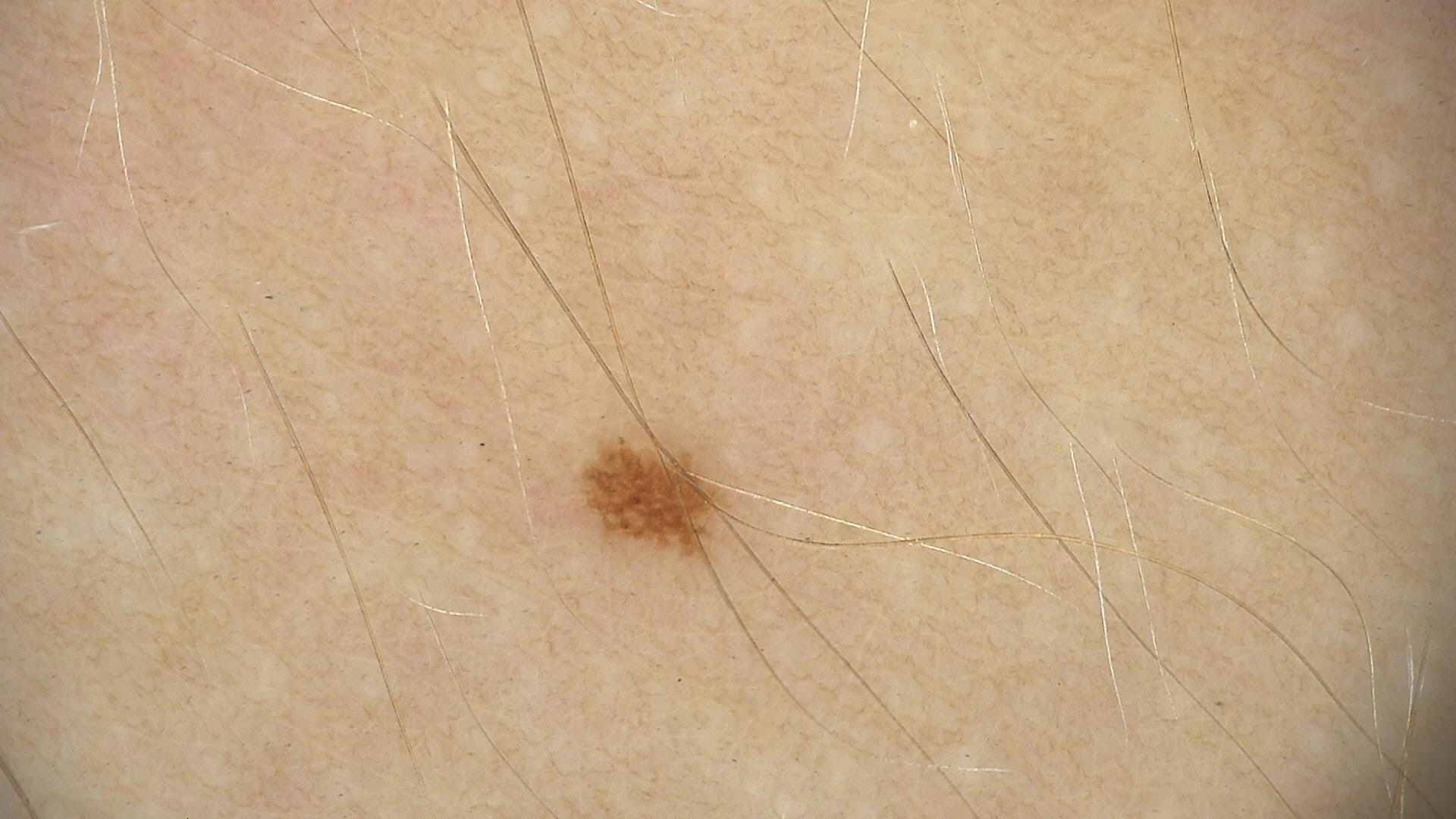Conclusion:
Labeled as a dysplastic junctional nevus.